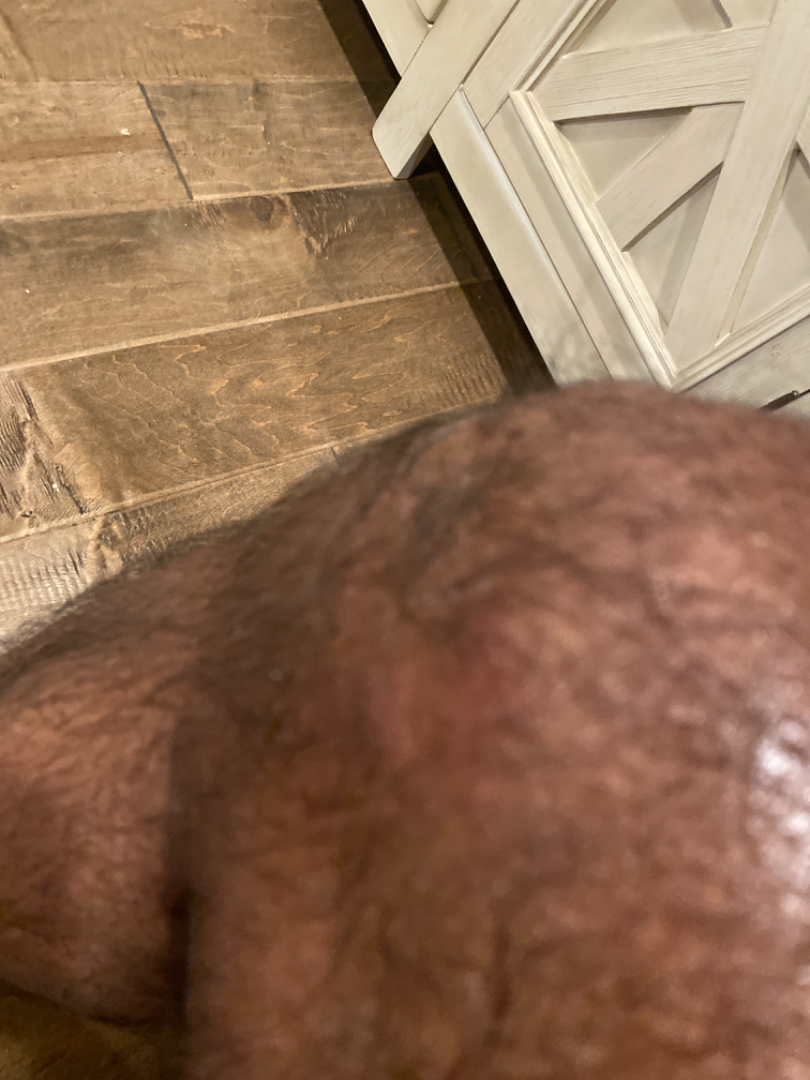The reviewer was unable to grade this case for skin condition. This image was taken at an angle. No relevant systemic symptoms. Reported lesion symptoms include darkening and itching. Texture is reported as raised or bumpy and fluid-filled. The leg is involved. The contributor reports the condition has been present for less than one week.